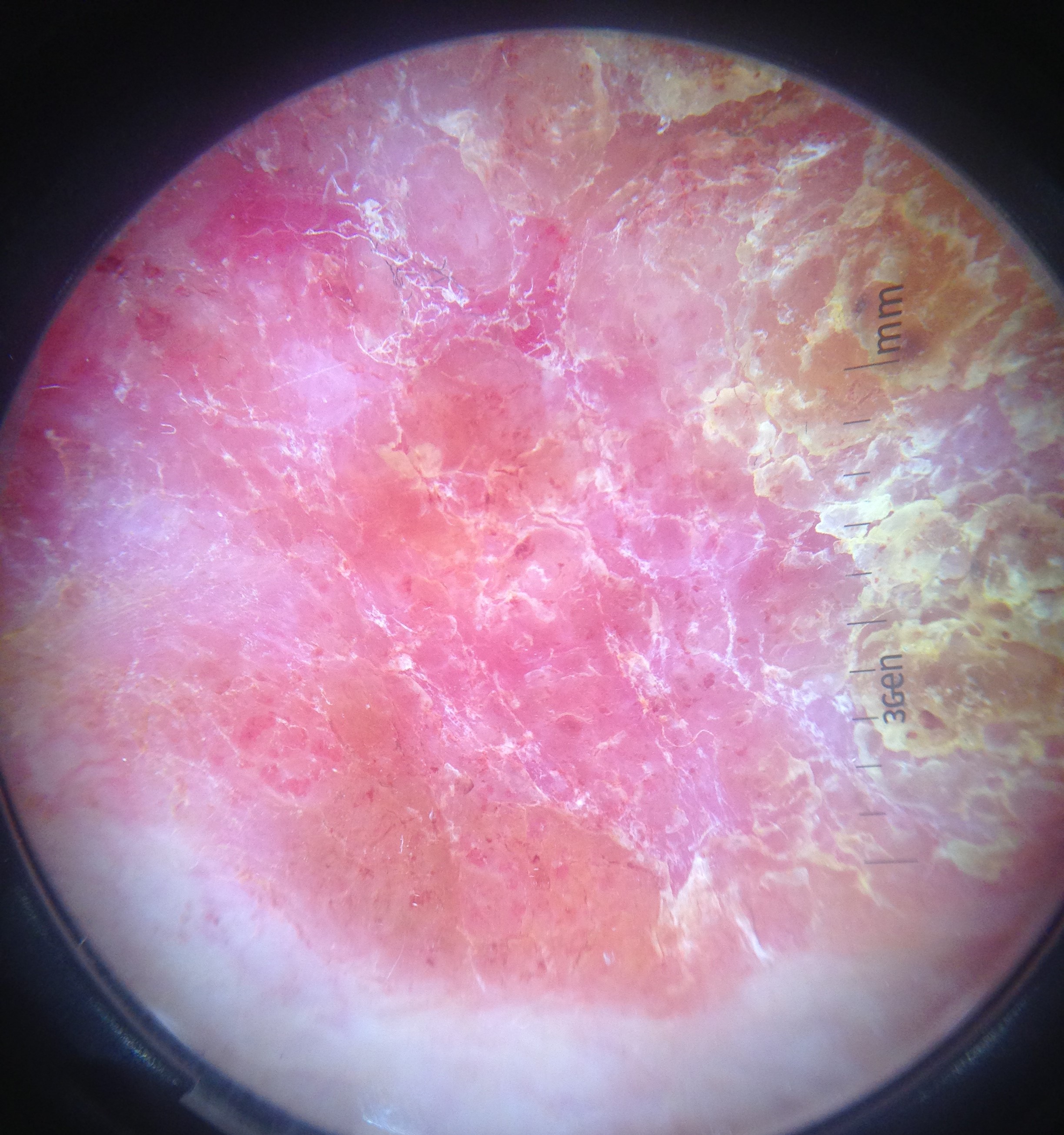label = Bowen's disease (biopsy-proven).